The subject is female · the photograph was taken at a distance · the lesion is associated with itching, bothersome appearance, enlargement and bleeding · no associated systemic symptoms reported · the lesion involves the front of the torso and arm · the contributor notes the lesion is raised or bumpy and rough or flaky · reported duration is one to three months · self-categorized by the patient as a rash:
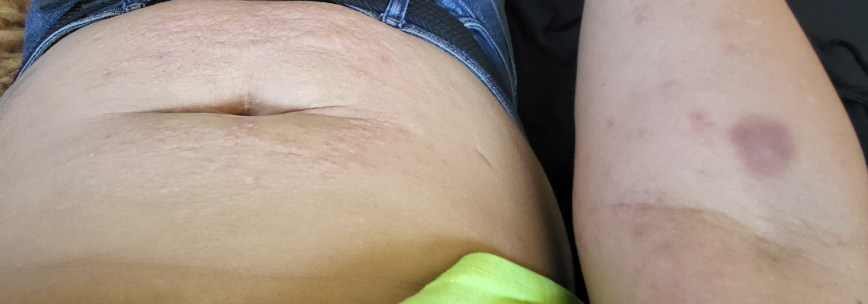On remote dermatologist review, the leading consideration is Lichen Simplex Chronicus; less probable is Eczema; lower on the differential is Psoriasis.